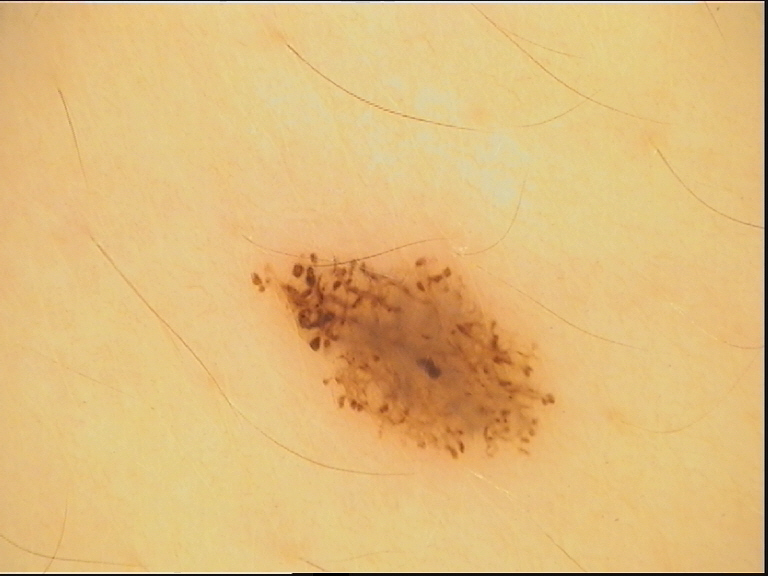class = dysplastic junctional nevus (expert consensus)